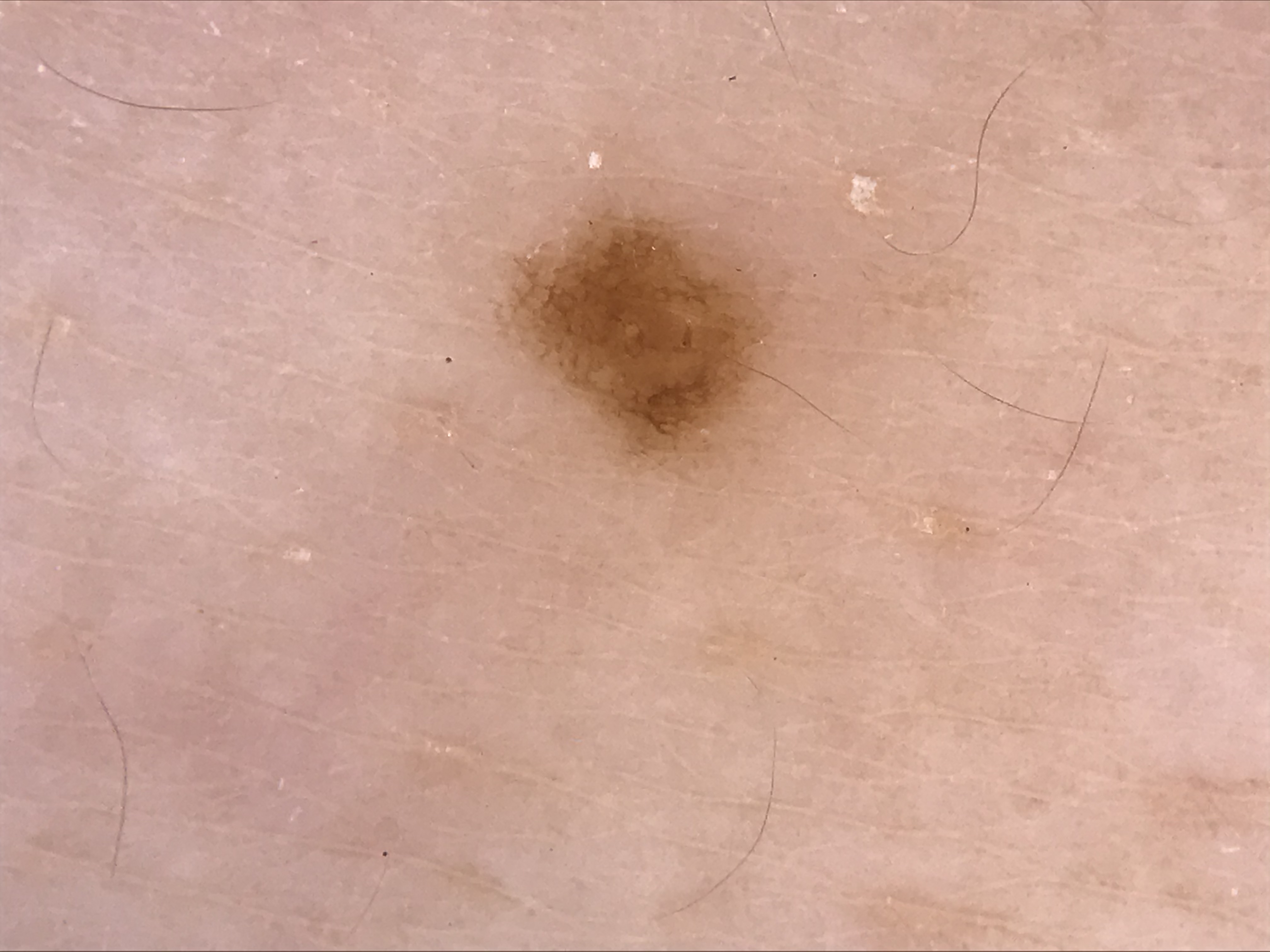Summary: Dermoscopy of a skin lesion. This is a banal lesion. Conclusion: The diagnostic label was a junctional nevus.